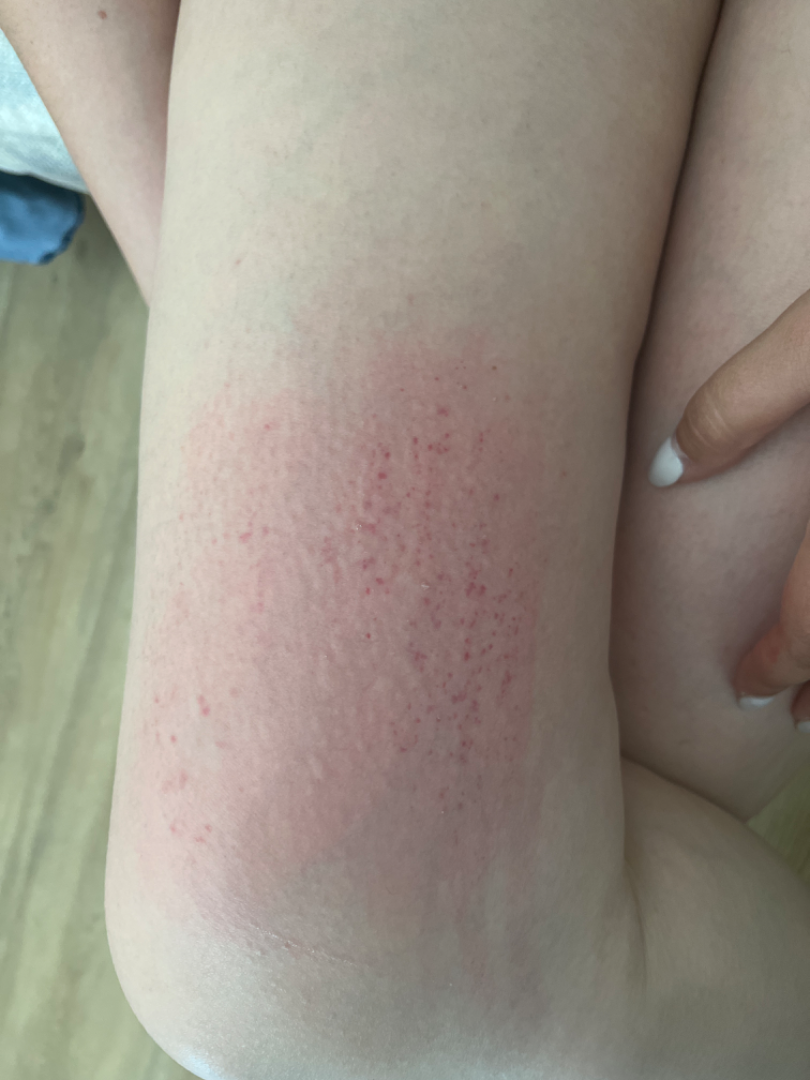surface texture = raised or bumpy | constitutional symptoms = none reported | anatomic site = leg | photo taken = close-up | clinical impression = most consistent with Eczema; an alternative is Acute dermatitis, NOS.